The lesion involves the arm. An image taken at an angle.
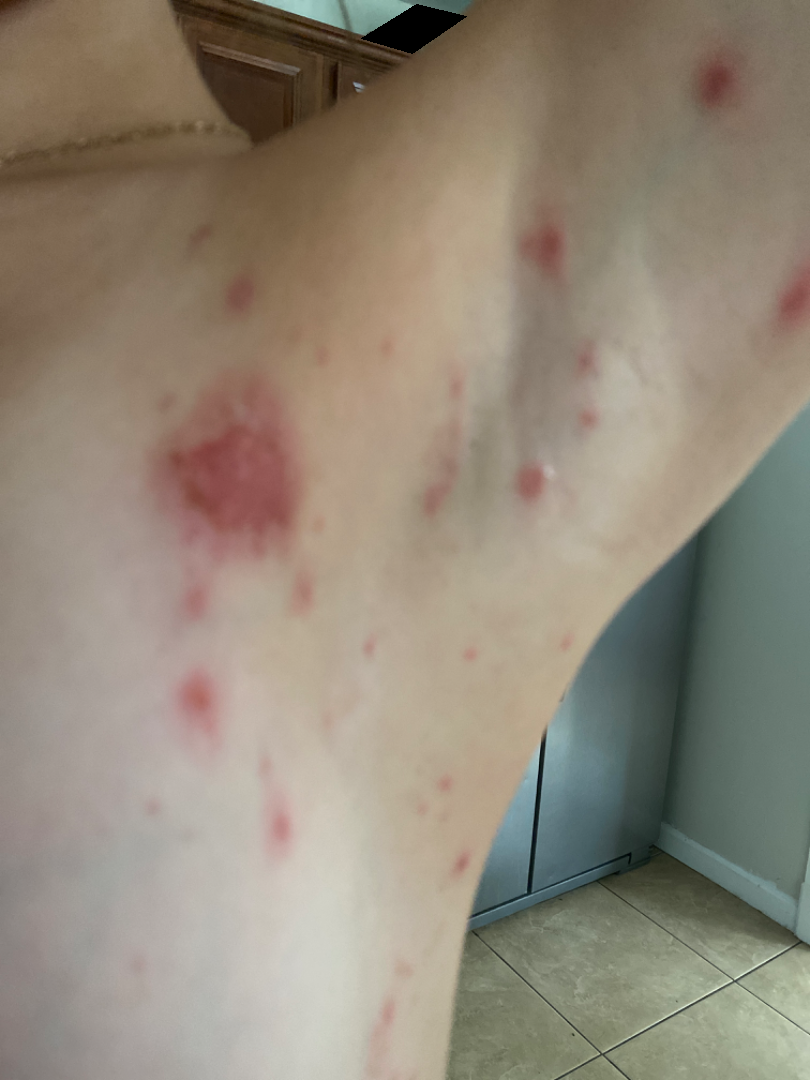Assessment: Impetigo (100%).